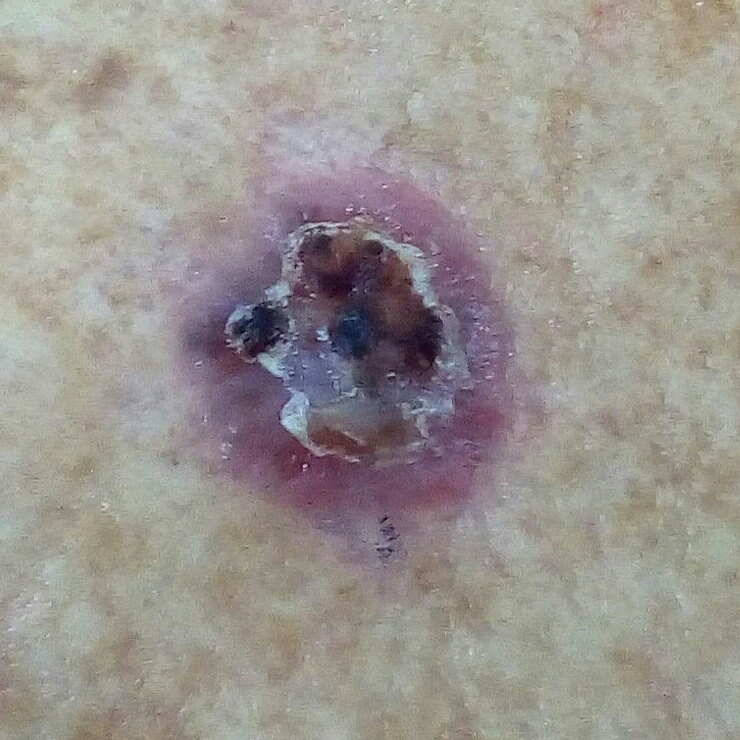The biopsy diagnosis was a basal cell carcinoma.